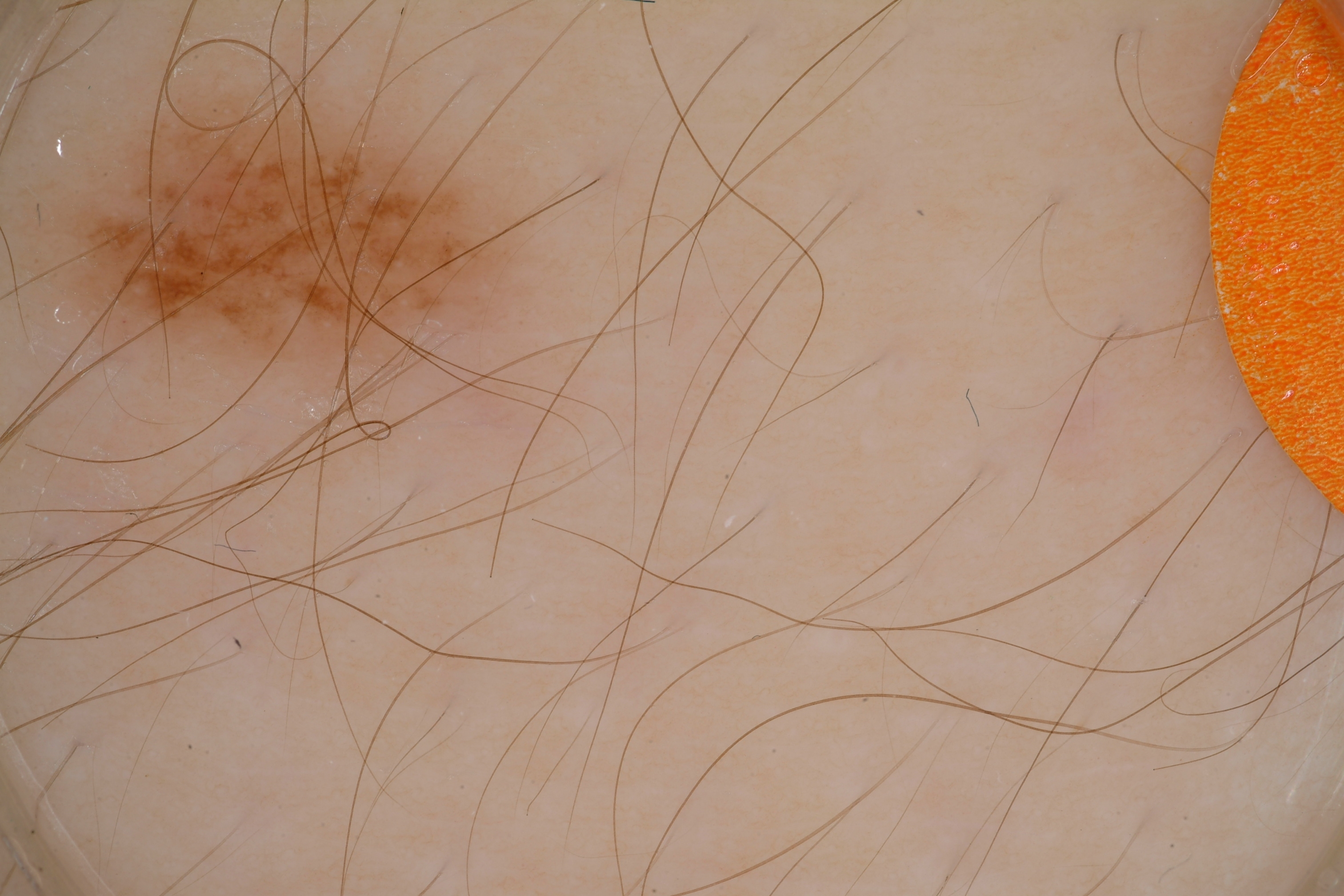| field | value |
|---|---|
| patient | male, roughly 15 years of age |
| modality | dermoscopy |
| dermoscopic features | pigment network |
| lesion location | x1=63 y1=85 x2=523 y2=387 |
| assessment | a melanocytic nevus |